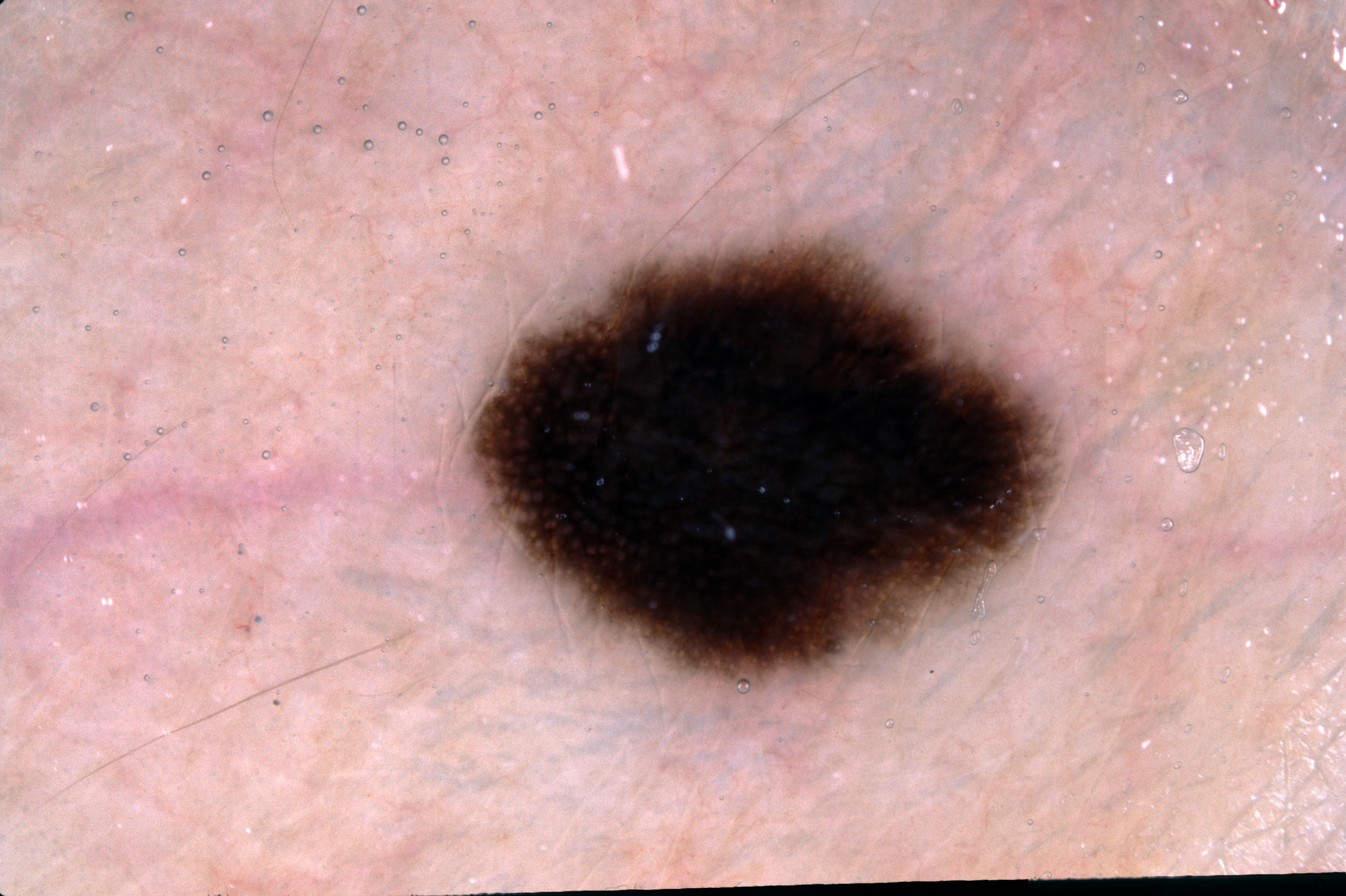Case summary:
A dermatoscopic image of a skin lesion. A female subject, in their 50s. As (left, top, right, bottom), the lesion's extent is bbox=[468, 237, 1059, 685]. On dermoscopy, the lesion shows pigment network. The lesion takes up about 15% of the image.
Impression:
The clinical diagnosis was a melanocytic nevus.